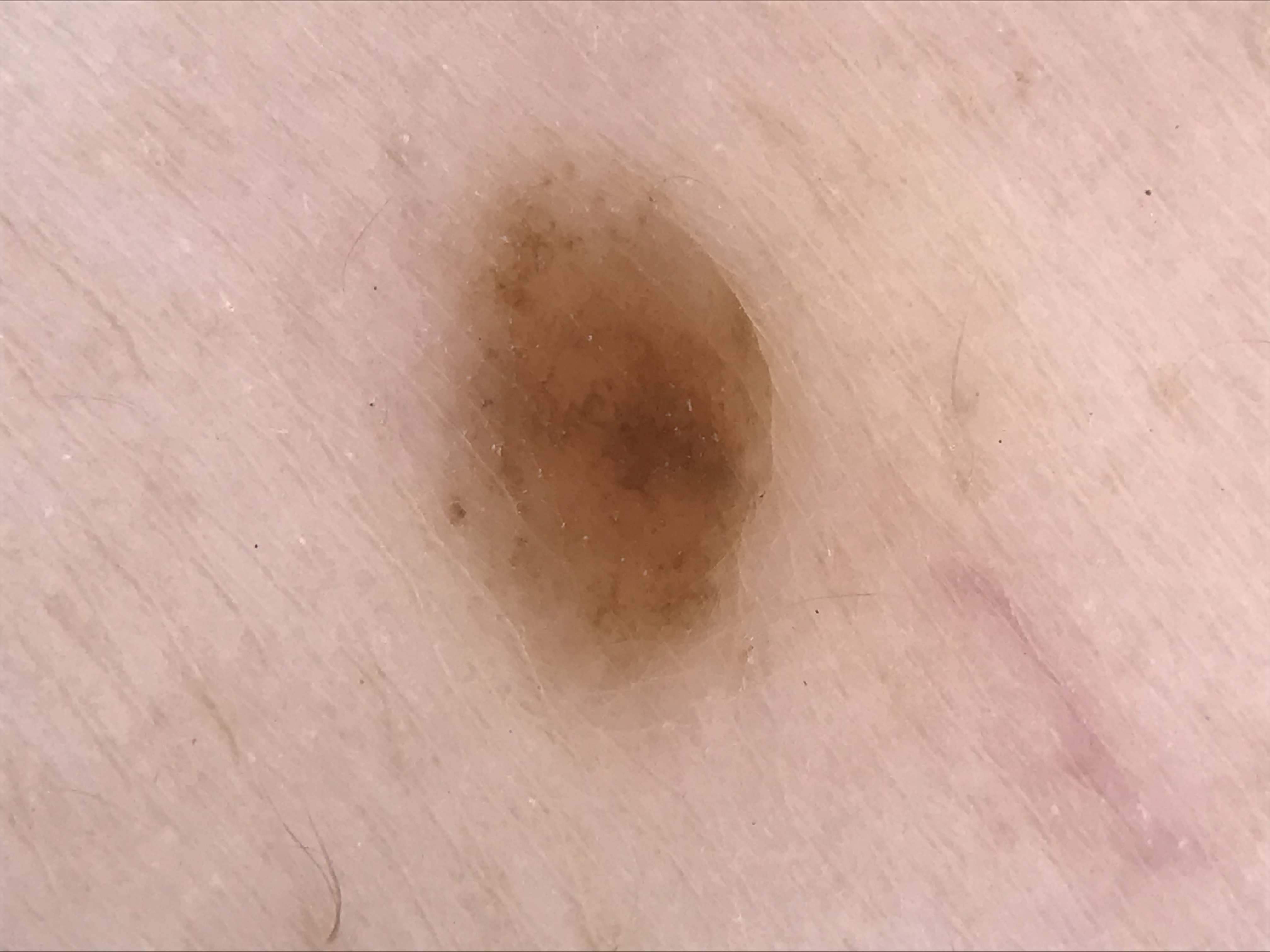image: dermatoscopy | diagnosis: dermal nevus (expert consensus).